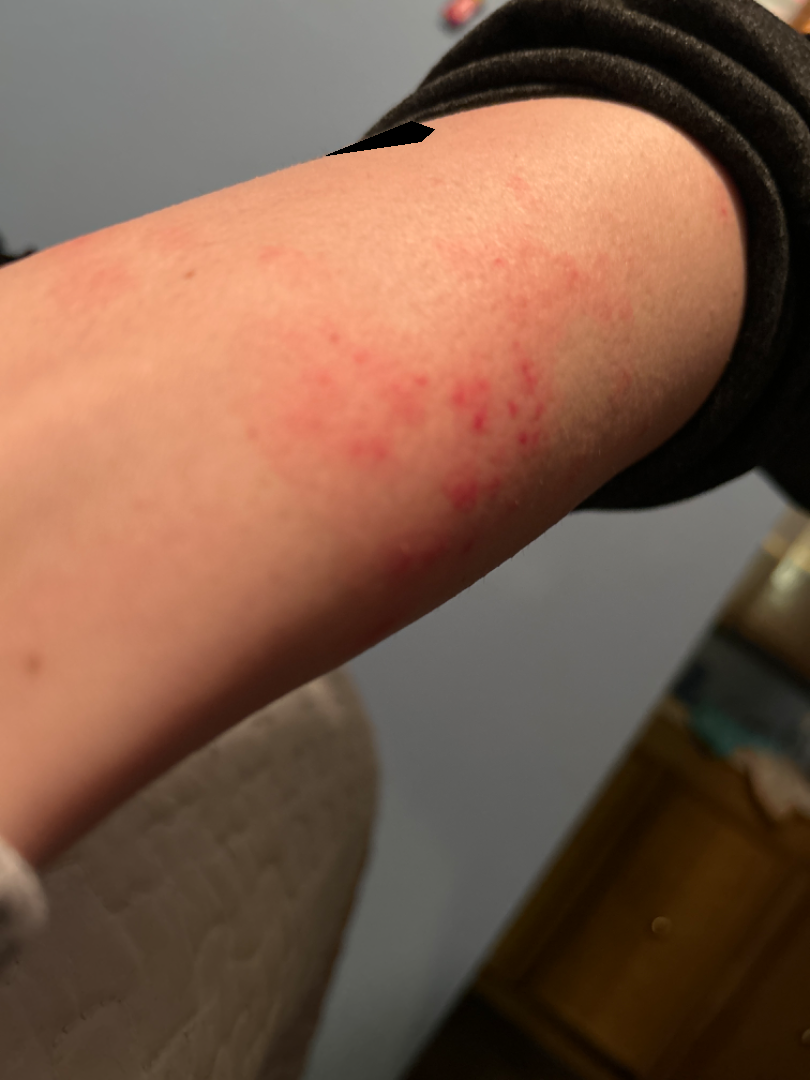On dermatologist assessment of the image: Folliculitis and Acute dermatitis, NOS were each considered, in no particular order.